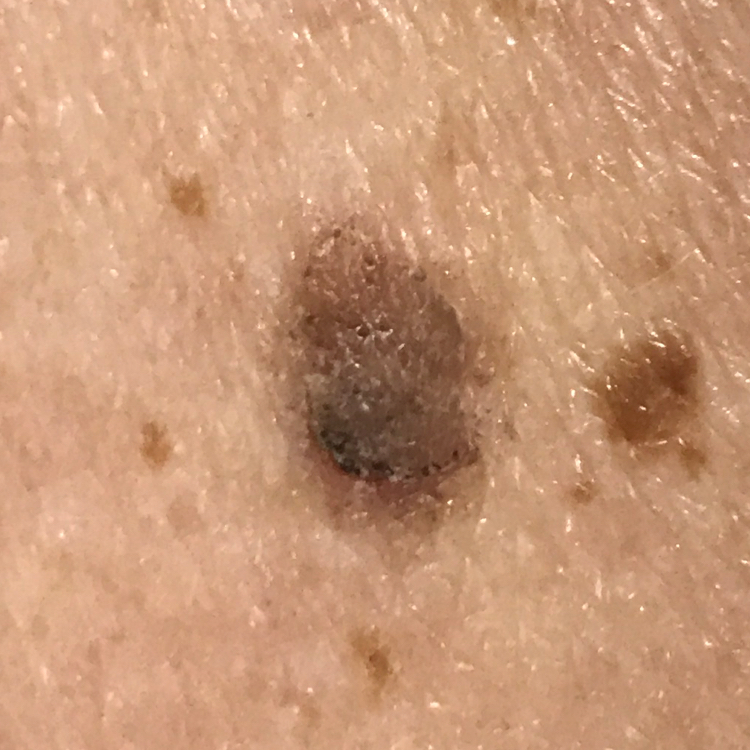image = clinical photo | site = the back | reported symptoms = elevation, itching, growth | diagnostic label = seborrheic keratosis (clinical consensus).